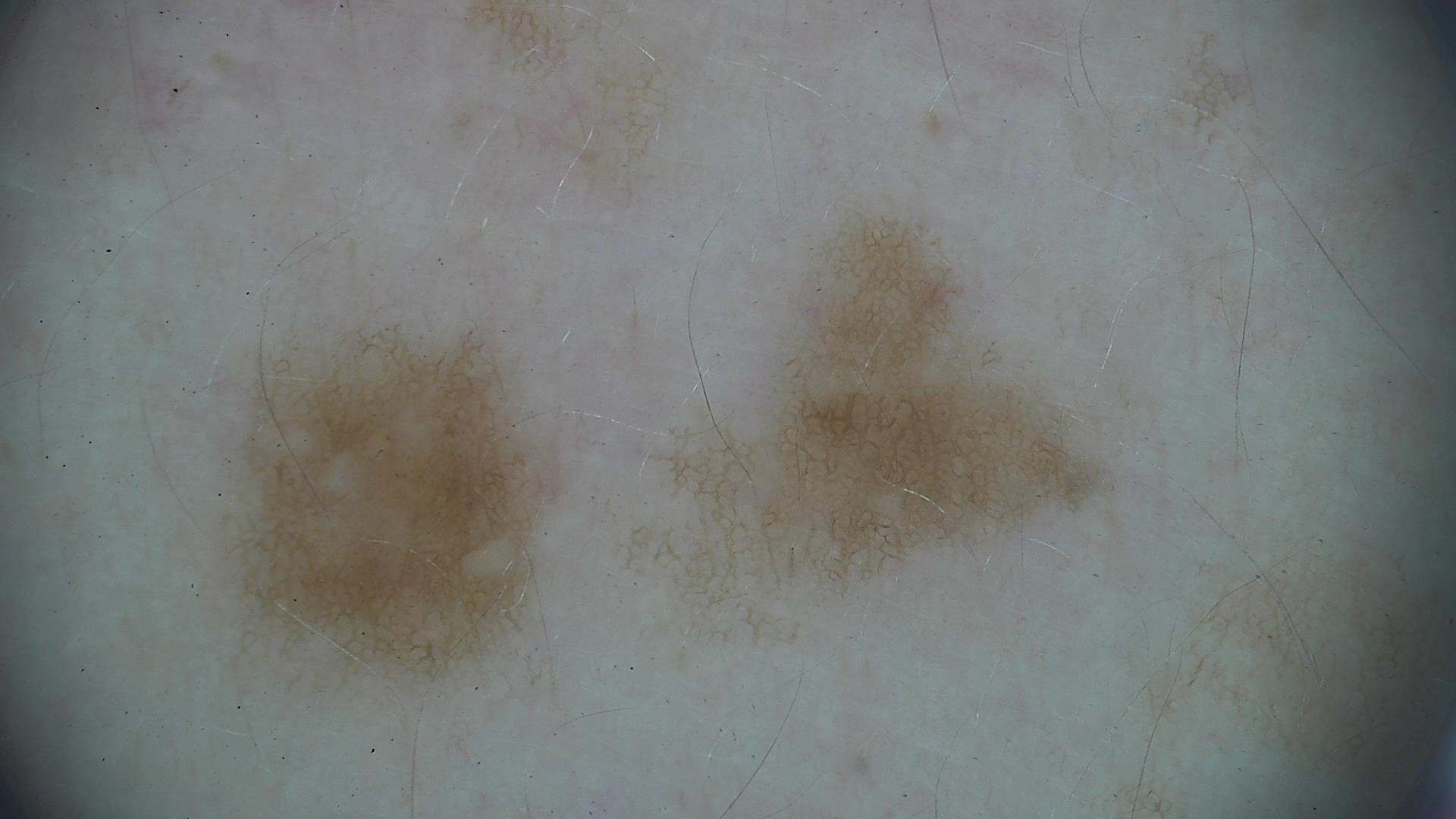modality: dermatoscopy
diagnostic label: dysplastic junctional nevus (expert consensus)